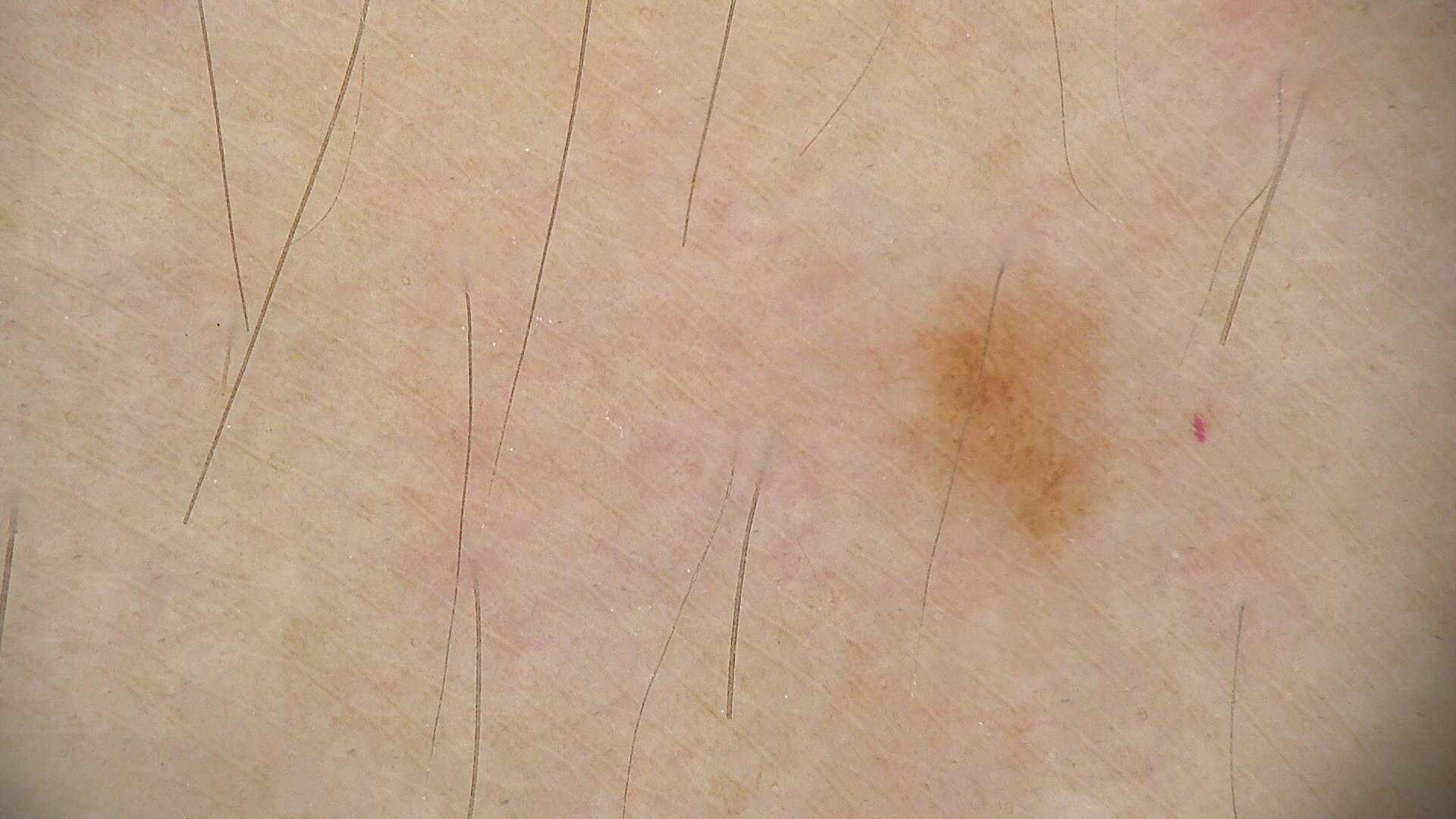image: dermatoscopy, label: dysplastic junctional nevus (expert consensus).